A male subject age 34. The patient is skin type III. A clinical photograph showing a skin lesion:
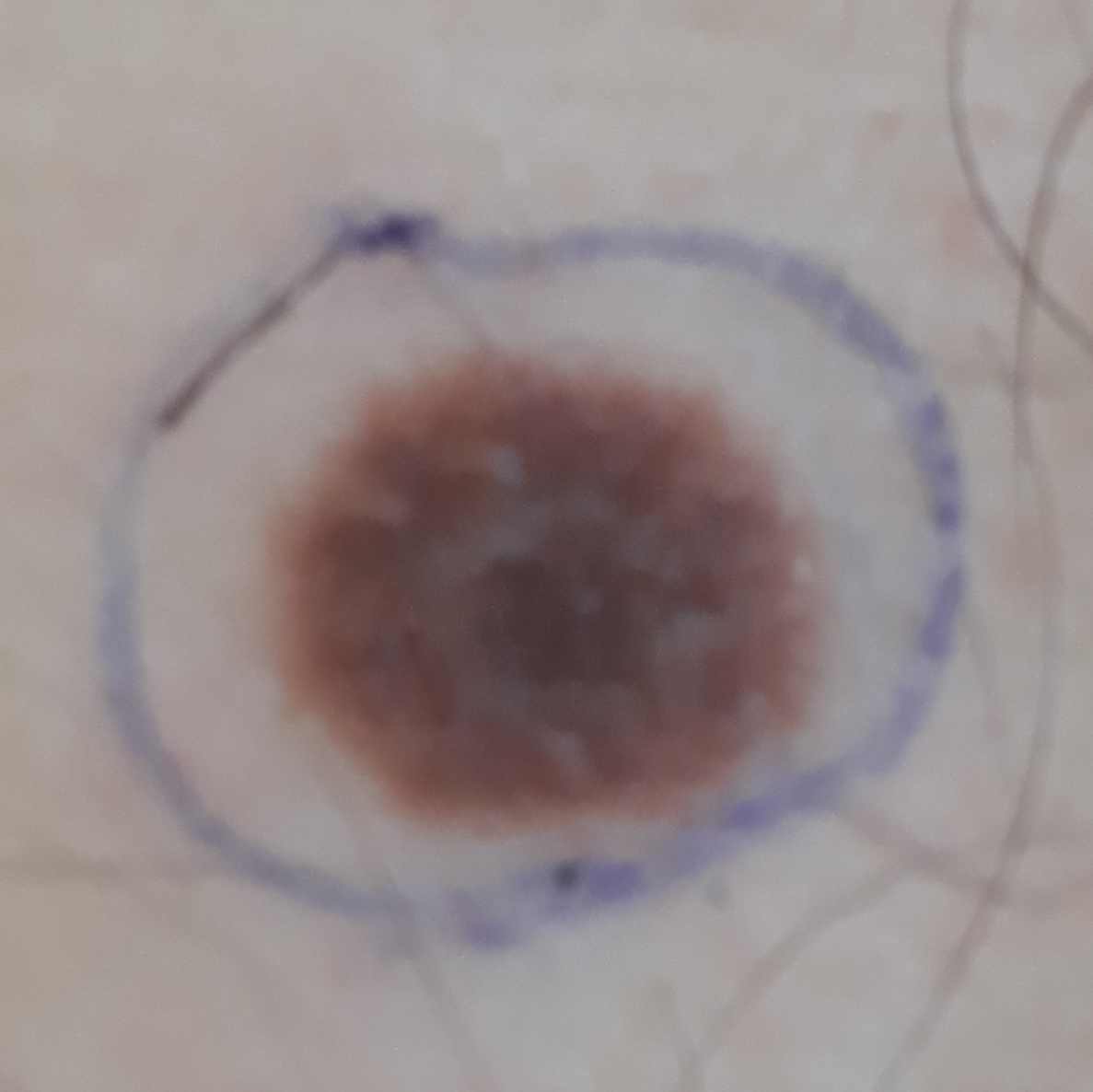Clinical context: Located on the abdomen. Measuring about 10 × 10 mm. The patient reports that the lesion has not bled and is not elevated. Diagnosis: Biopsy-confirmed as a benign skin lesion — a nevus.